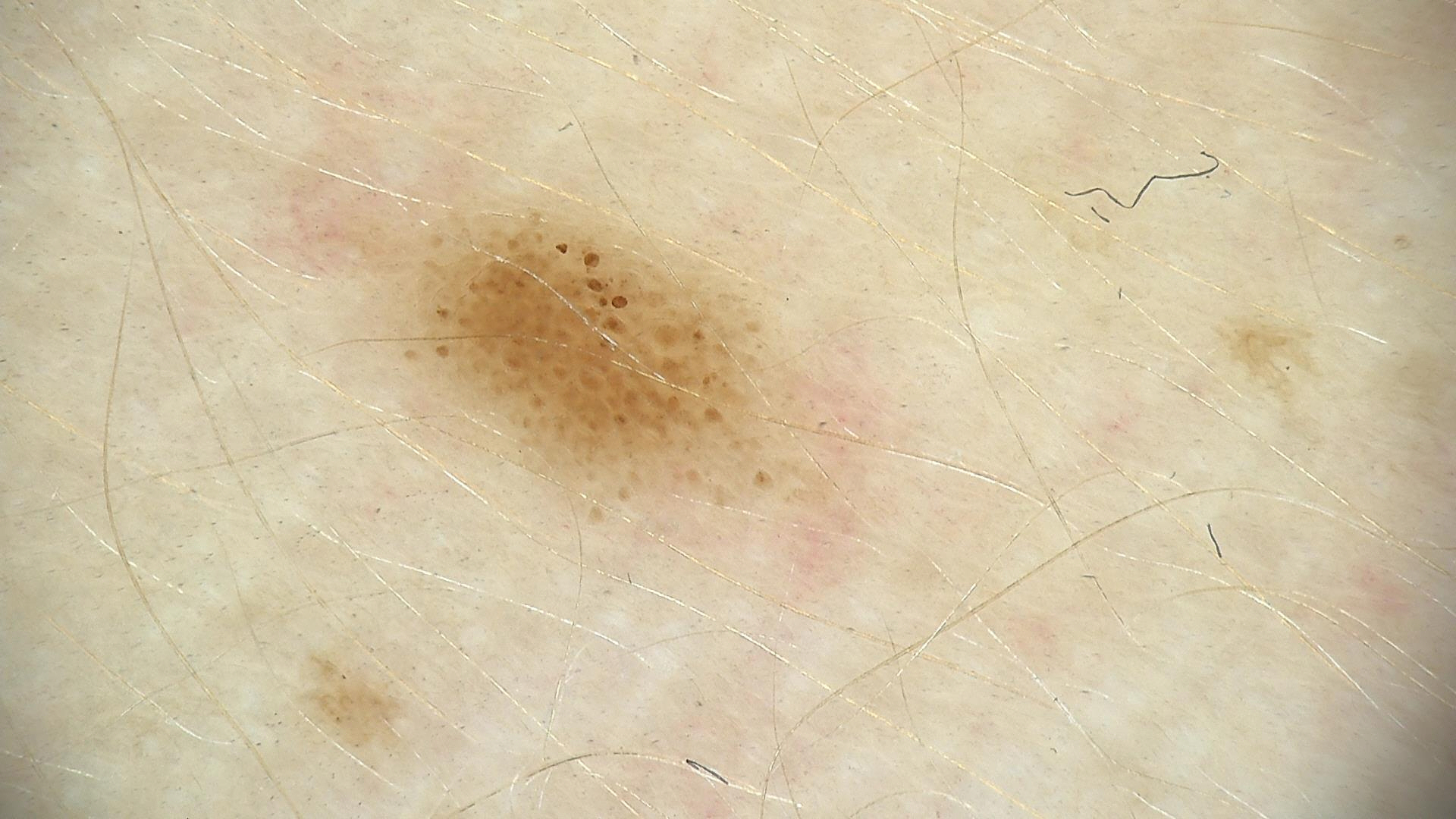image type: dermoscopy; class: dysplastic junctional nevus (expert consensus).